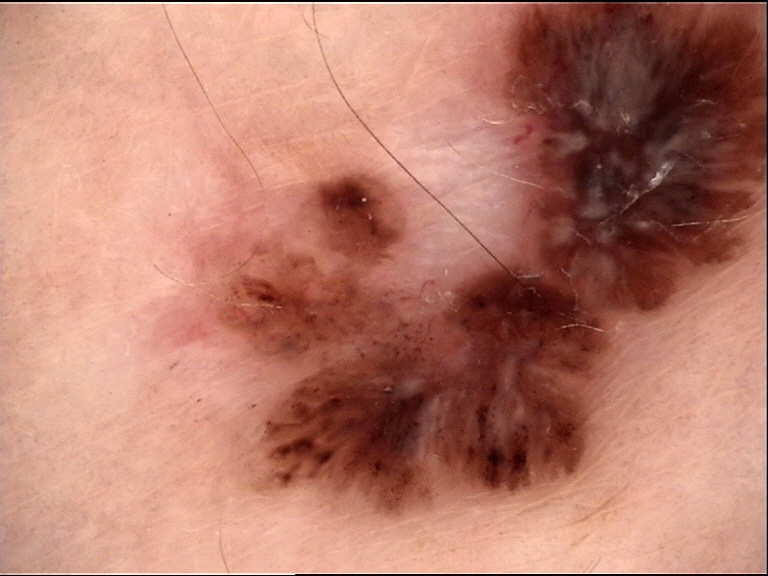| field | value |
|---|---|
| label | basal cell carcinoma (biopsy-proven) |